Collected as part of a research study, without a referral diagnosis · a female patient 78 years of age.
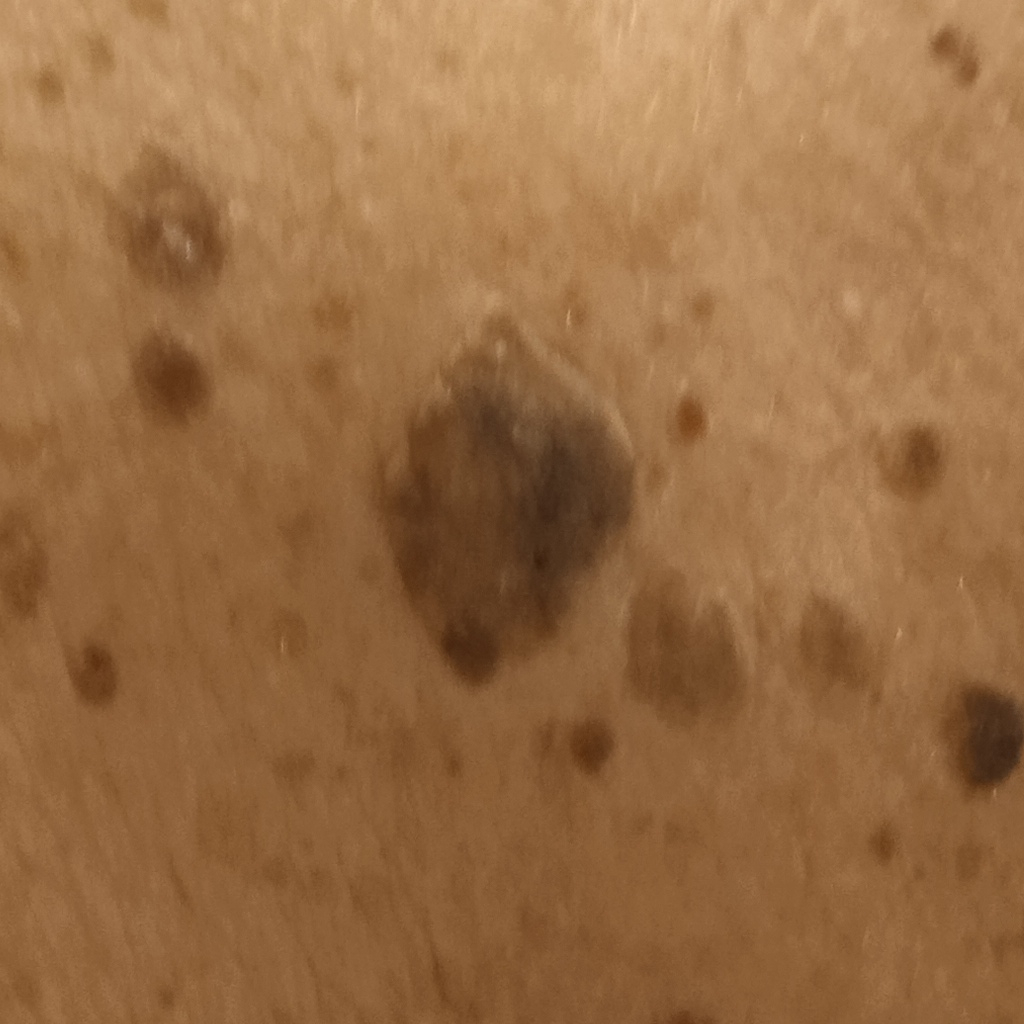Q: How large is the lesion?
A: 15.7 mm
Q: What was the diagnosis?
A: seborrheic keratosis (dermatologist consensus)